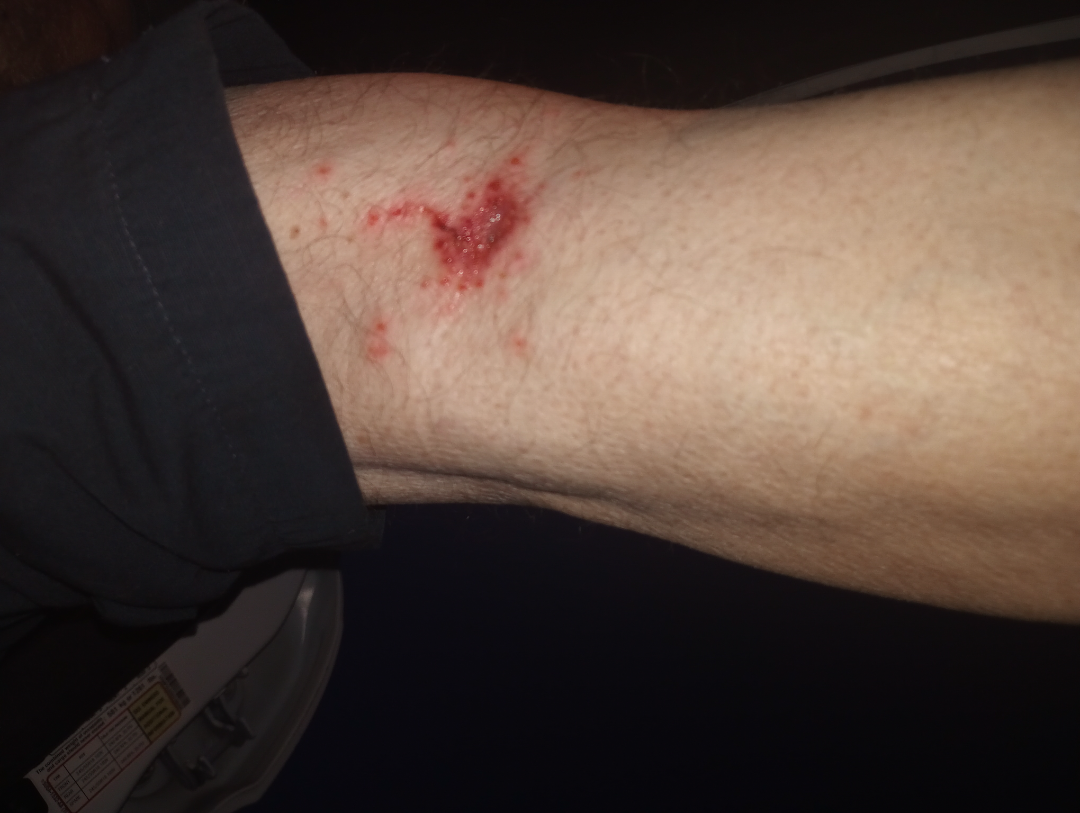The subject is a male aged 60–69. The photo was captured at a distance. The lesion is described as raised or bumpy and rough or flaky. The affected area is the leg. On dermatologist assessment of the image, the impression was split between Impetigo and Herpes Zoster; a more distant consideration is Infected eczema.